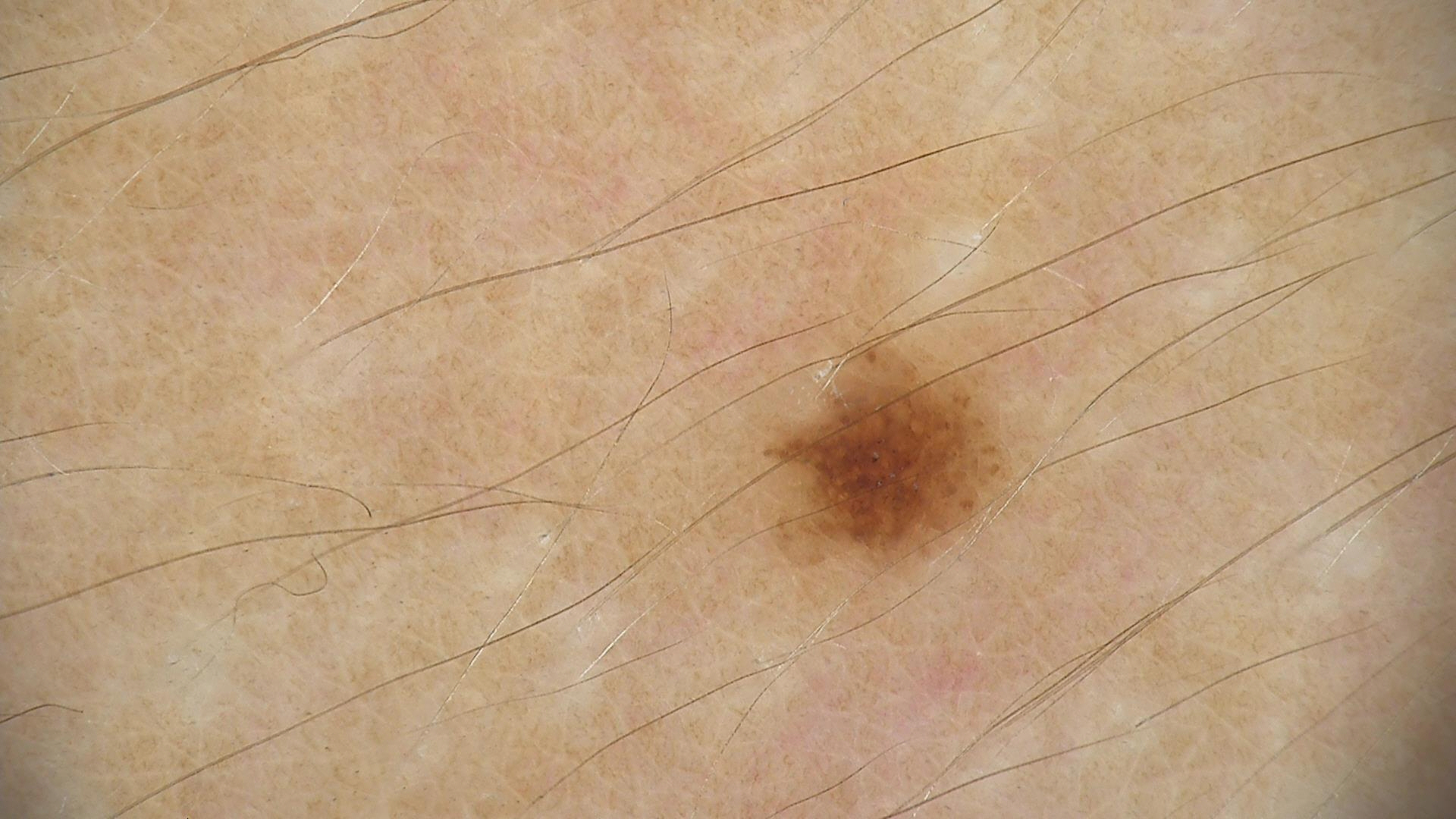{"diagnosis": {"name": "dysplastic junctional nevus", "code": "jd", "malignancy": "benign", "super_class": "melanocytic", "confirmation": "expert consensus"}}